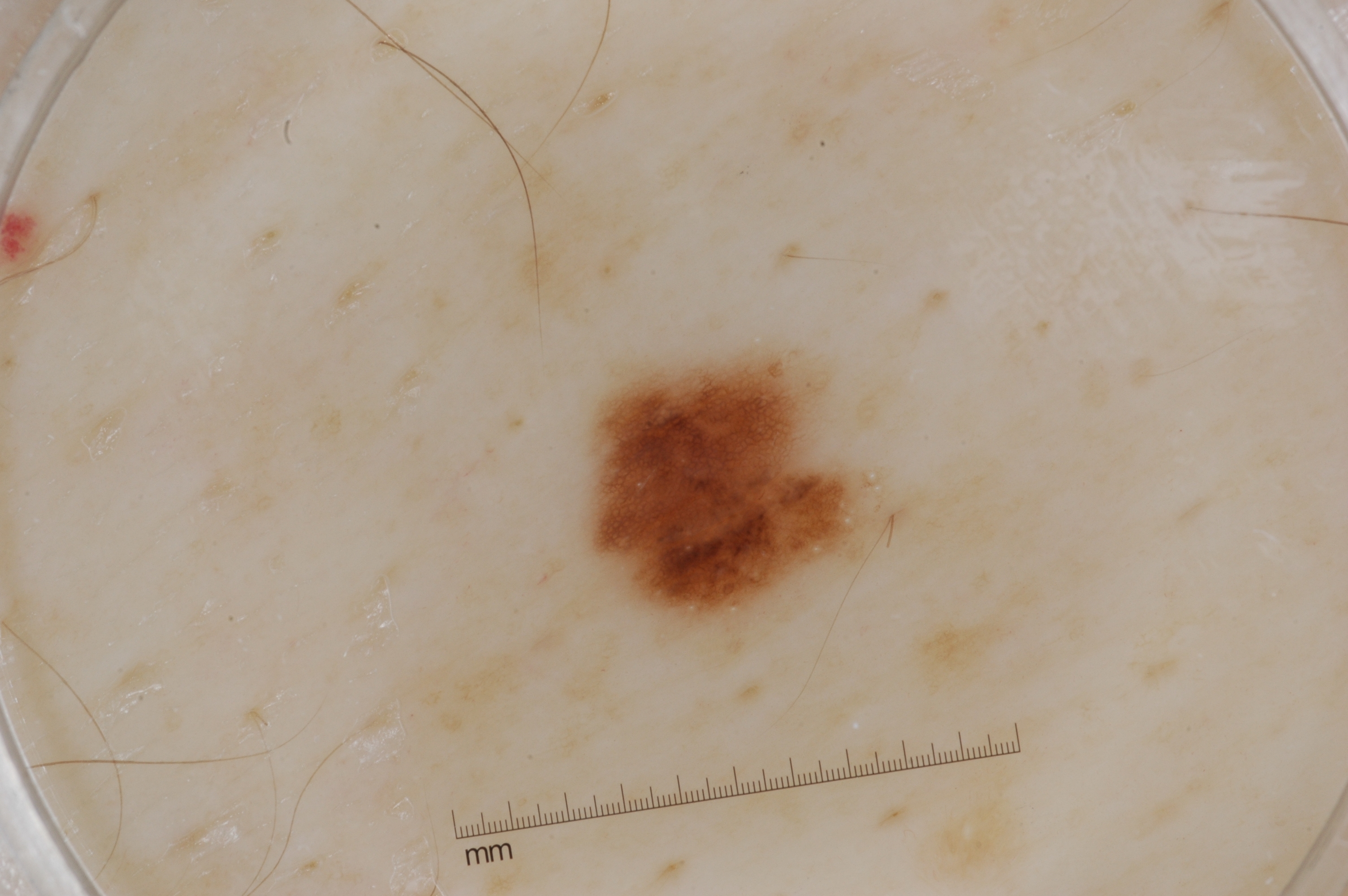Findings: A dermoscopic view of a skin lesion. The dermoscopic pattern shows milia-like cysts and pigment network; no negative network or streaks. The lesion is located at bbox=[590, 350, 885, 630]. A small lesion within a wider field of skin. Assessment: Consistent with a melanocytic nevus, a benign skin lesion.